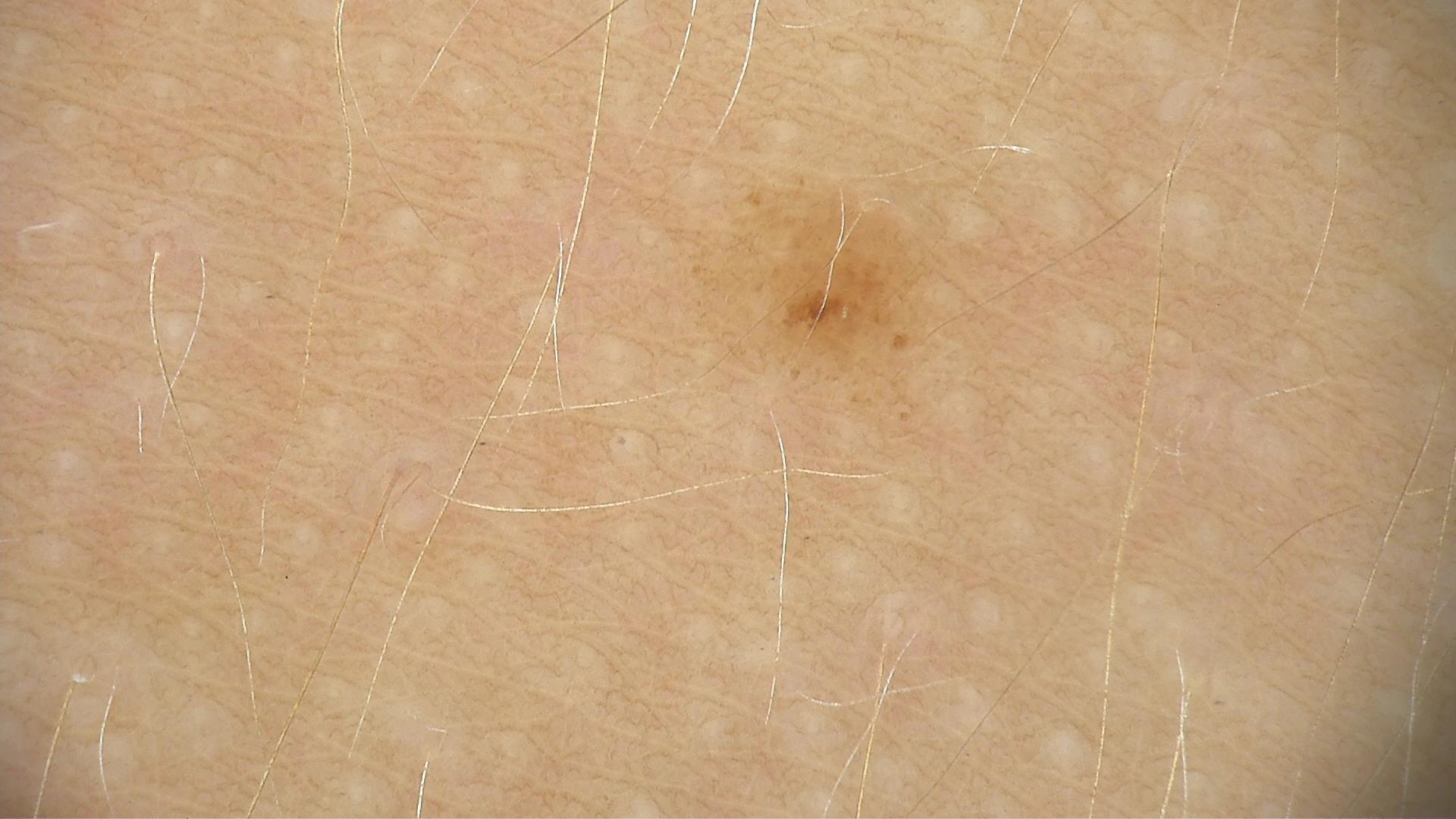Q: What was the diagnostic impression?
A: dysplastic junctional nevus (expert consensus)